A subject 63 years old · a clinical close-up photograph of a skin lesion: 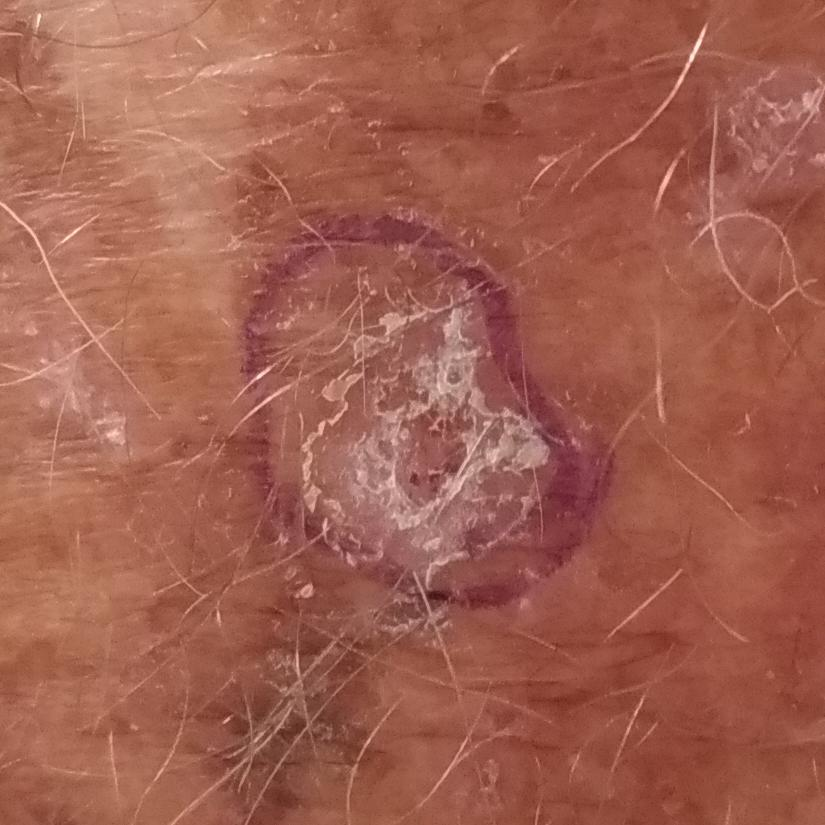  lesion_location: a forearm
  symptoms:
    present:
      - elevation
      - itching
    absent:
      - growth
  diagnosis:
    name: actinic keratosis
    code: ACK
    malignancy: indeterminate
    confirmation: clinical consensus